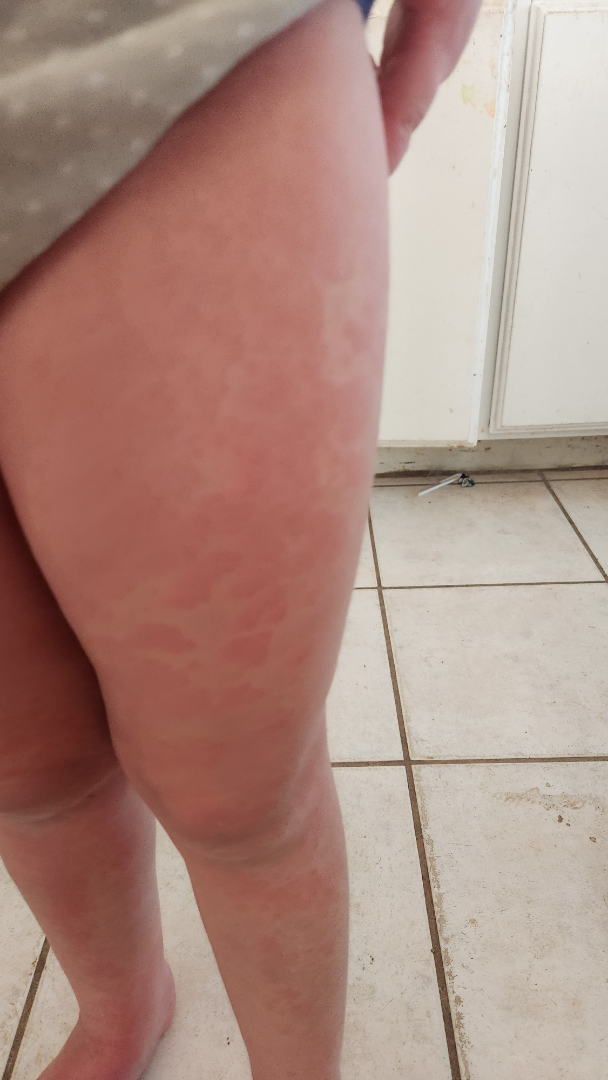Clinical context: The contributor is a female aged 18–29. The lesion is described as flat. Close-up view. Symptoms reported: pain and itching. The patient described the issue as a rash. Present for about one day. The affected area is the arm, front of the torso, leg, top or side of the foot and back of the torso. Assessment: On dermatologist assessment of the image: the impression is Urticaria.